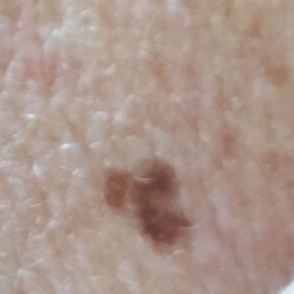Expert review favored a nevus.